A dermoscopy image of a single skin lesion.
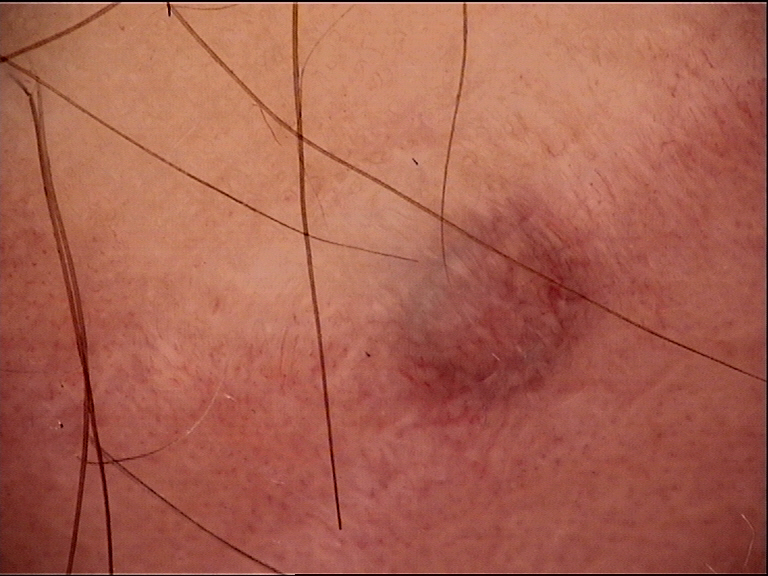The architecture is that of a banal, dermal lesion.
The diagnosis was a blue nevus.